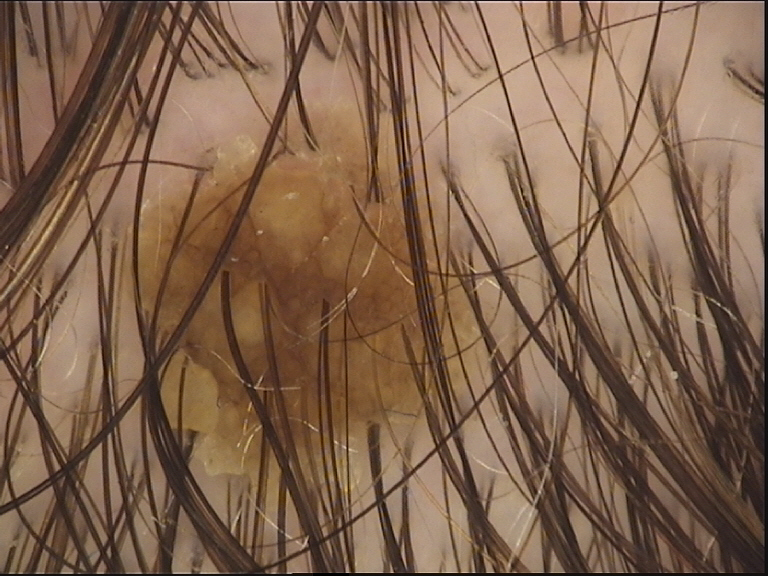lesion type=keratinocytic; class=seborrheic keratosis (expert consensus).